A close-up photograph. Located on the arm — 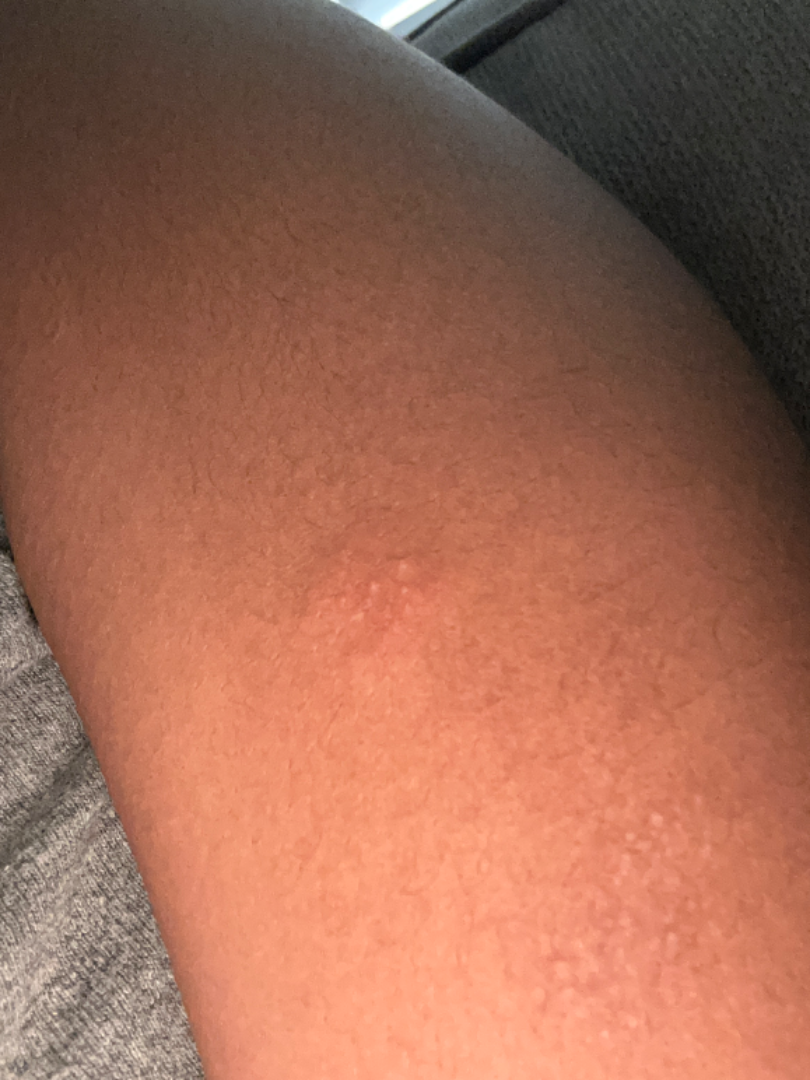On remote dermatologist review: most consistent with Eczema.